A female subject about 20 years old · a dermoscopic view of a skin lesion: 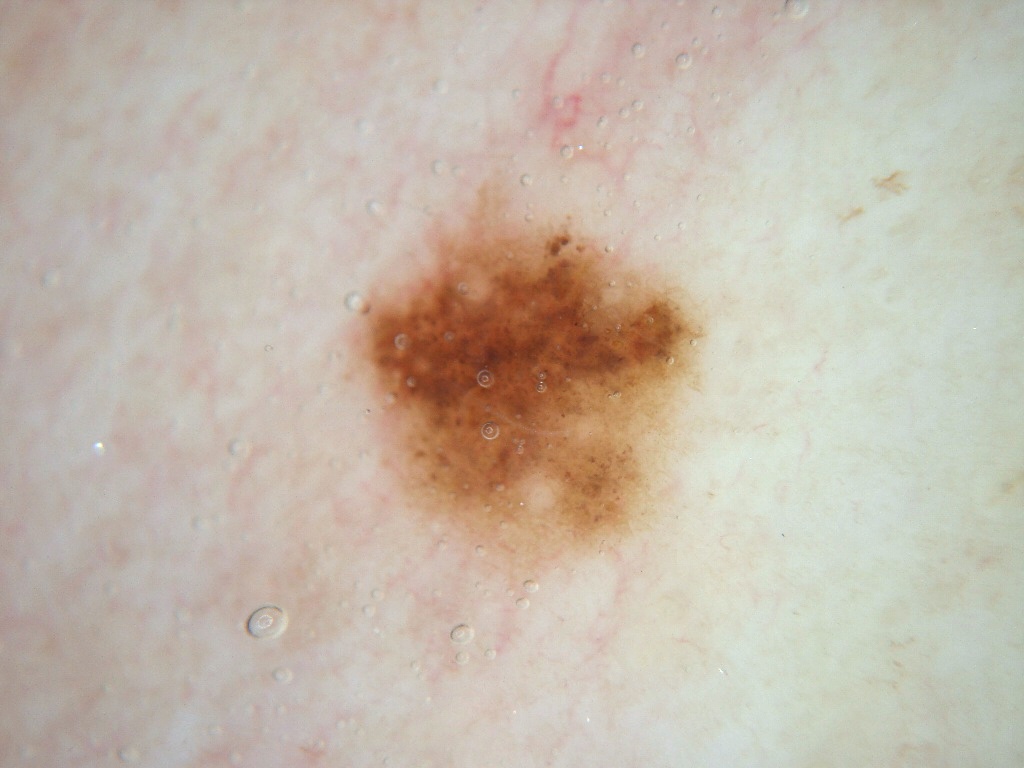In (x1, y1, x2, y2) order, the visible lesion spans <box>350, 185, 698, 561</box>. The dermoscopic pattern shows no pigment network, negative network, streaks, milia-like cysts, or globules. The diagnostic assessment was a melanocytic nevus, a benign lesion.